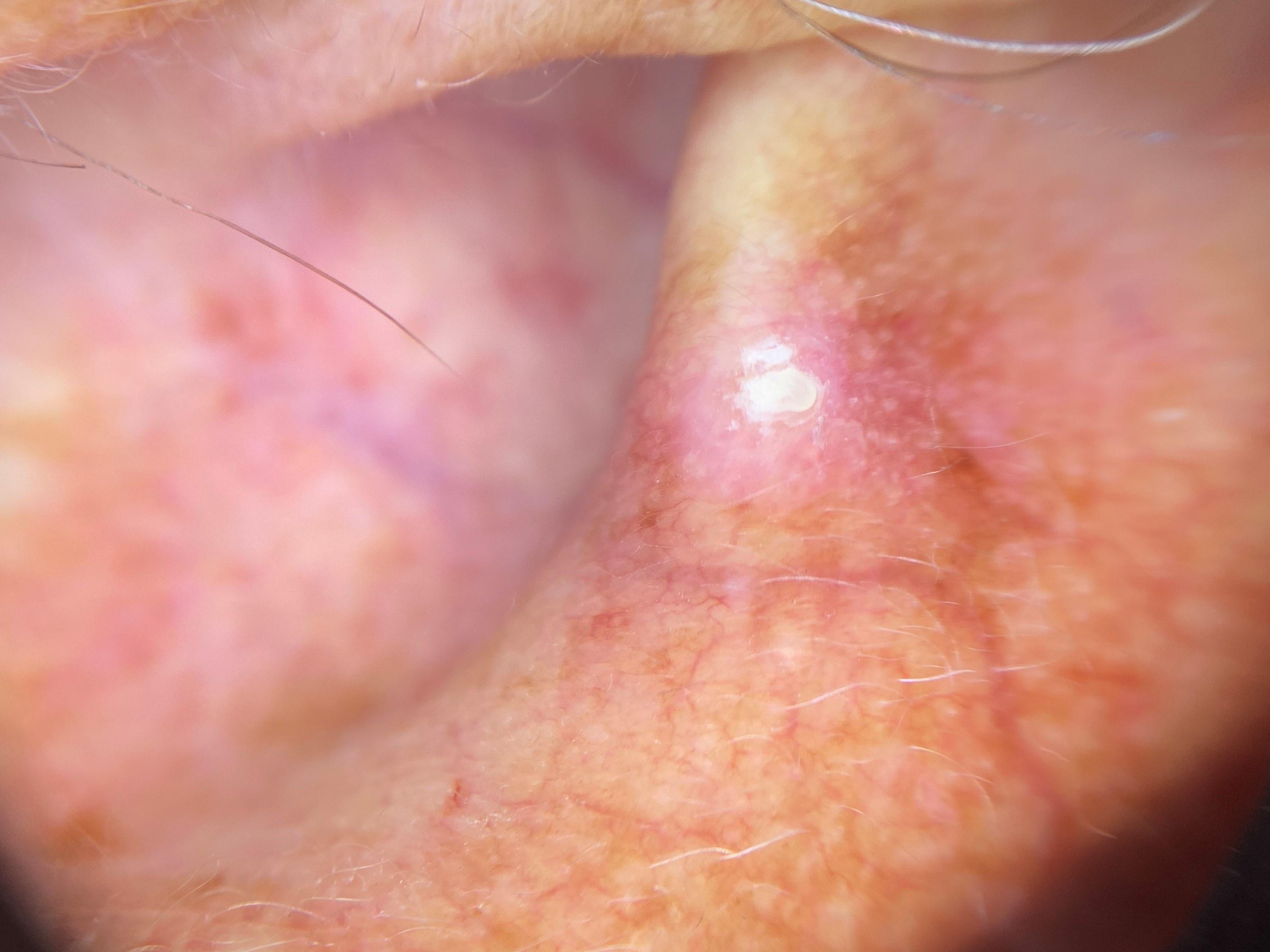diagnostic label=Solar or actinic keratosis (biopsy-proven)